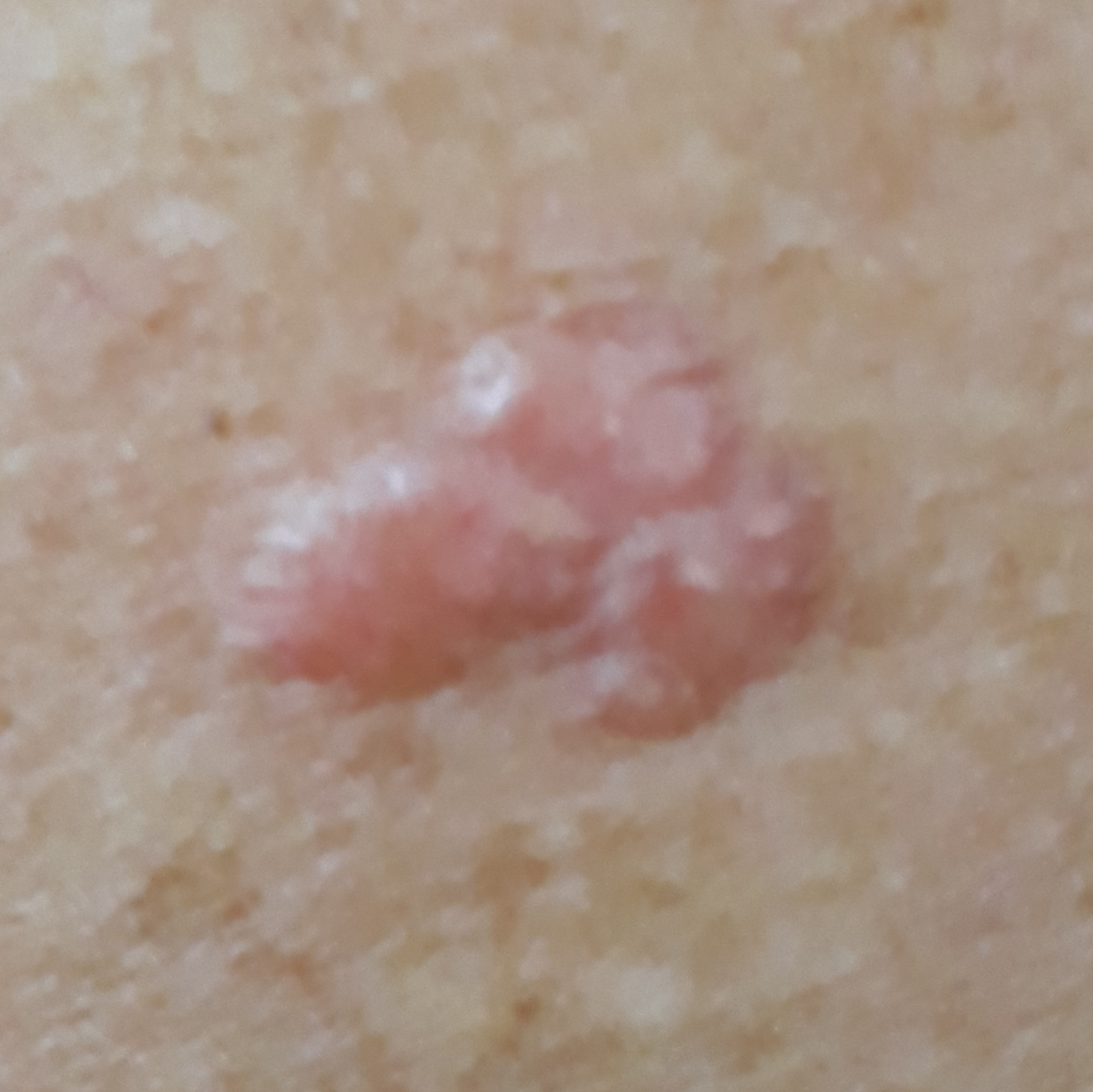History notes pesticide exposure and no alcohol use.
A male patient 74 years old.
The patient was assessed as FST II.
A smartphone photograph of a skin lesion.
The lesion is on an arm.
By the patient's account, the lesion itches and is elevated, but does not hurt.
Histopathological examination showed a basal cell carcinoma.